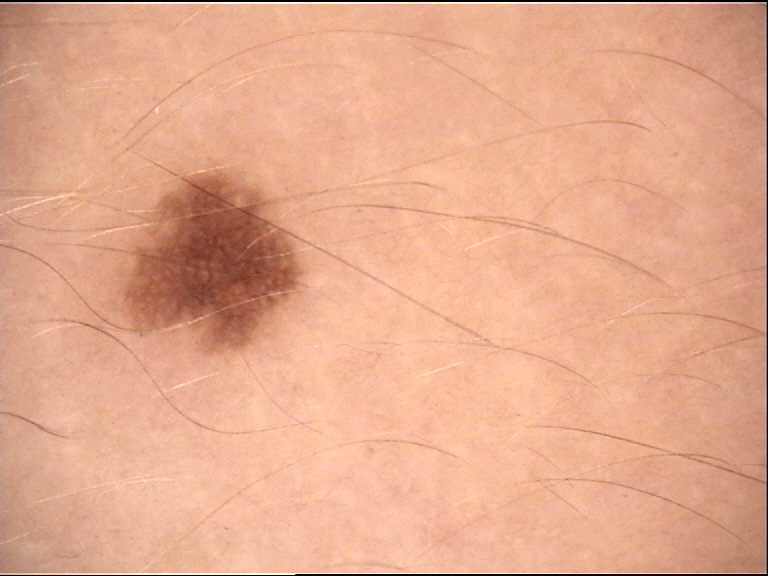assessment=junctional nevus (expert consensus).